Located on the arm, leg and back of the hand · the photograph is a close-up of the affected area:
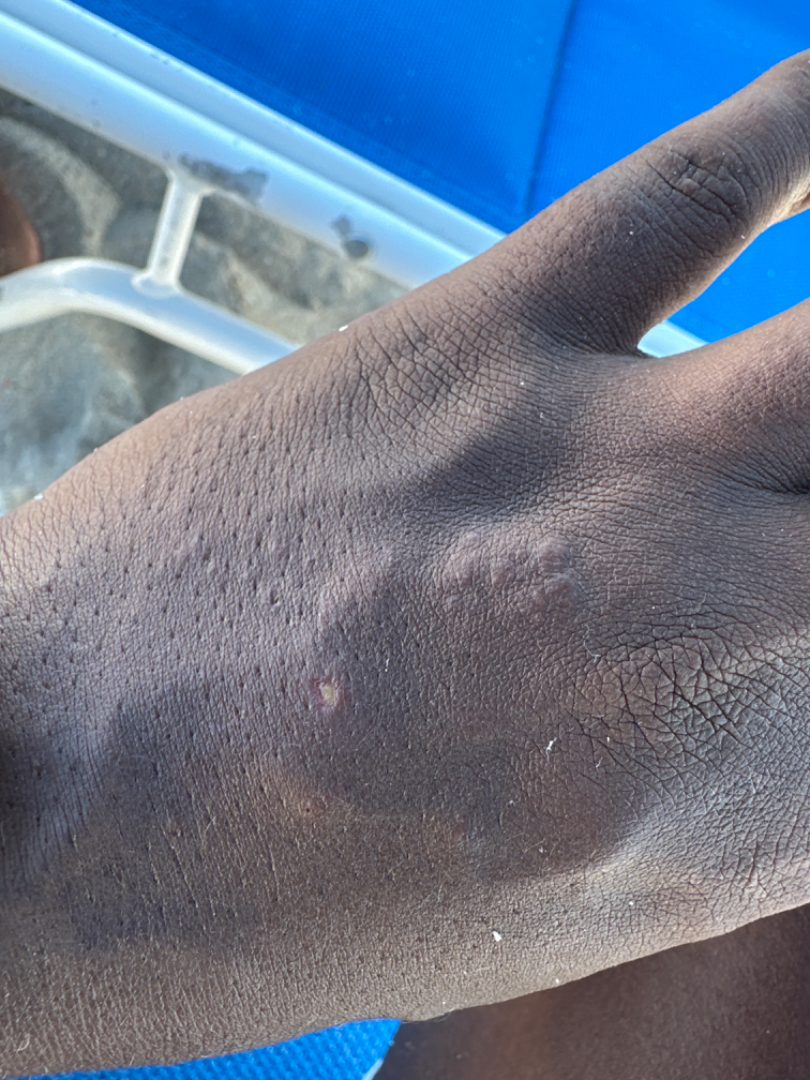{"assessment": "ungradable on photographic review"}